Texture is reported as raised or bumpy and rough or flaky. The condition has been present for less than one week. The leg is involved. Female patient, age 30–39. The photograph is a close-up of the affected area. Symptoms reported: itching and bothersome appearance: 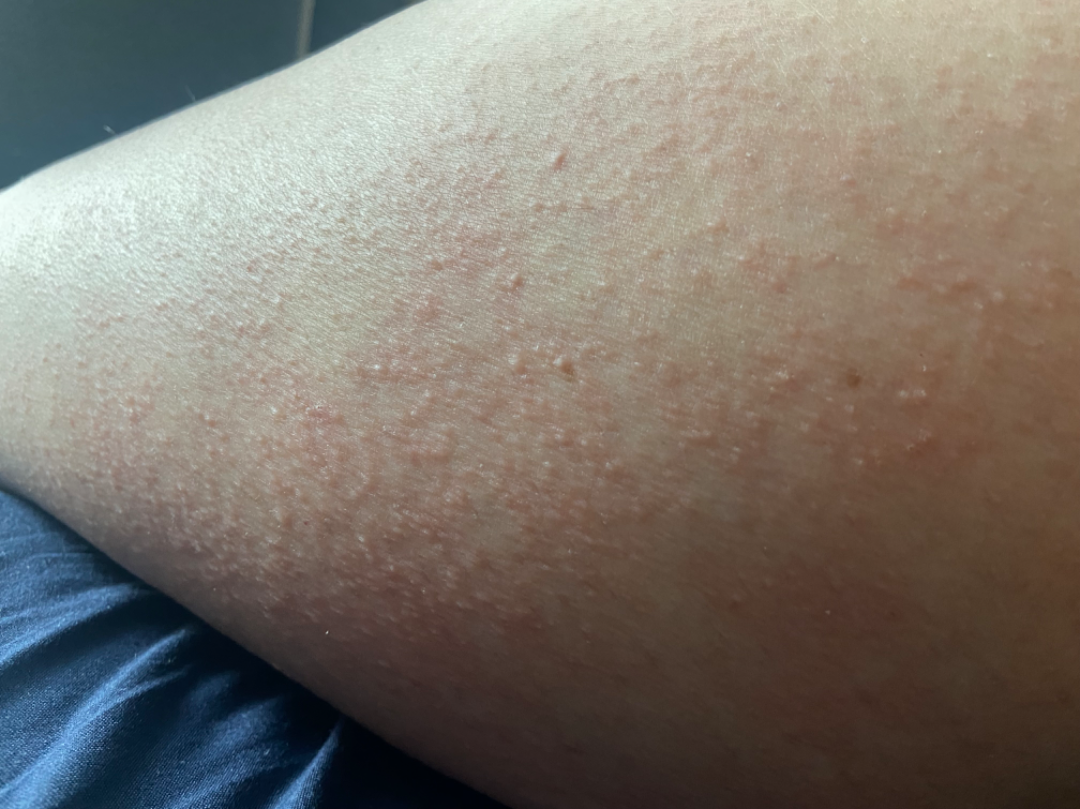The reviewing dermatologists' impression was: most likely Keratosis pilaris; also consider Eczema; lower on the differential is Miliaria; a remote consideration is Folliculitis.